A clinical close-up photograph of a skin lesion · Fitzpatrick phototype IV · the chart records alcohol use and prior malignancy (patient or family) · a female subject in their 20s.
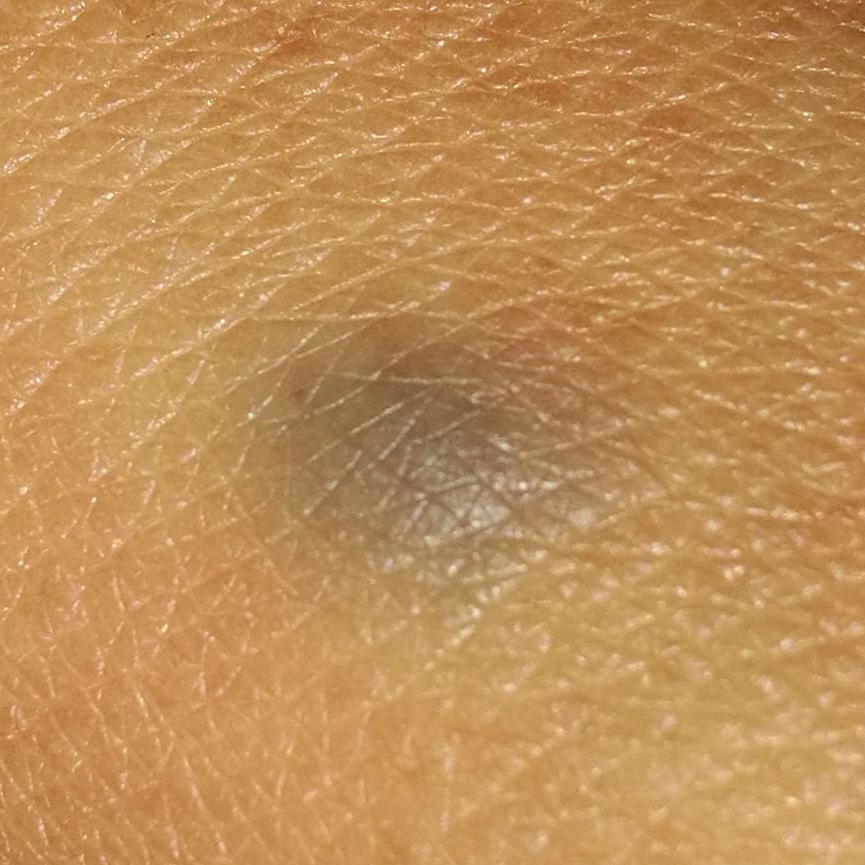Findings:
• region — a hand
• symptoms — none reported
• pathology — nevus (biopsy-proven)